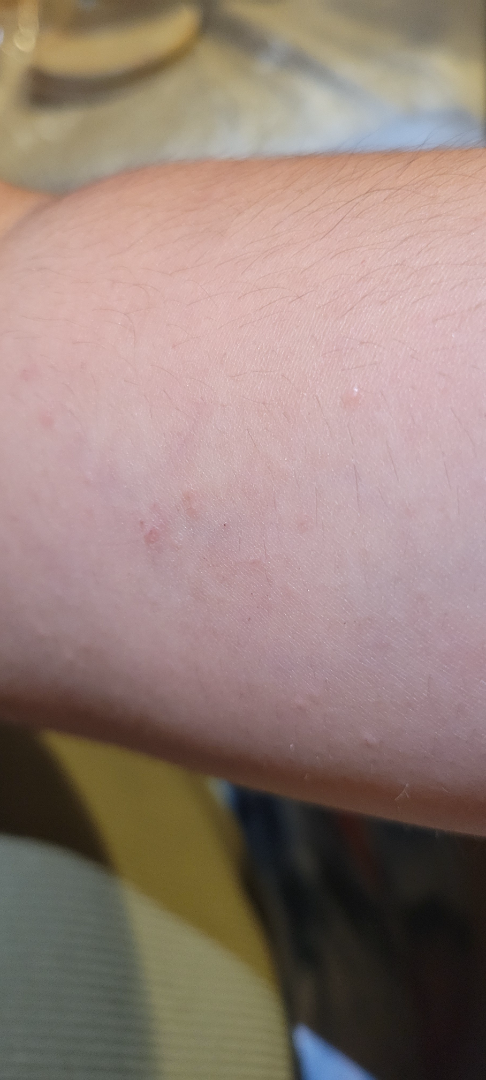Impression: Keratosis pilaris (considered); Eczema (considered).